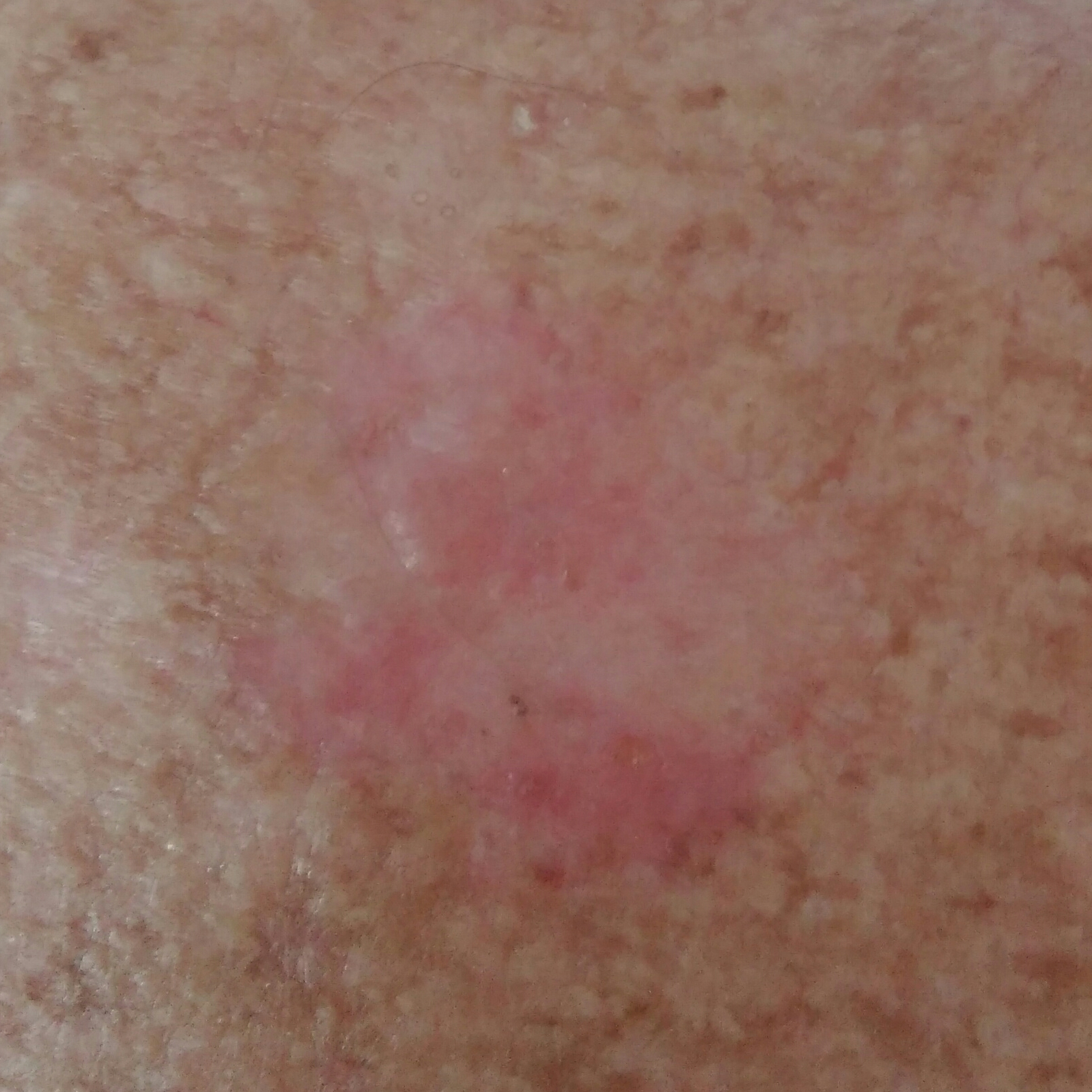| feature | finding |
|---|---|
| diagnostic label | squamous cell carcinoma (biopsy-proven) |